A clinical photograph of a skin lesion. Acquired for a research image collection, with no referral diagnosis. A female patient 59 years old: 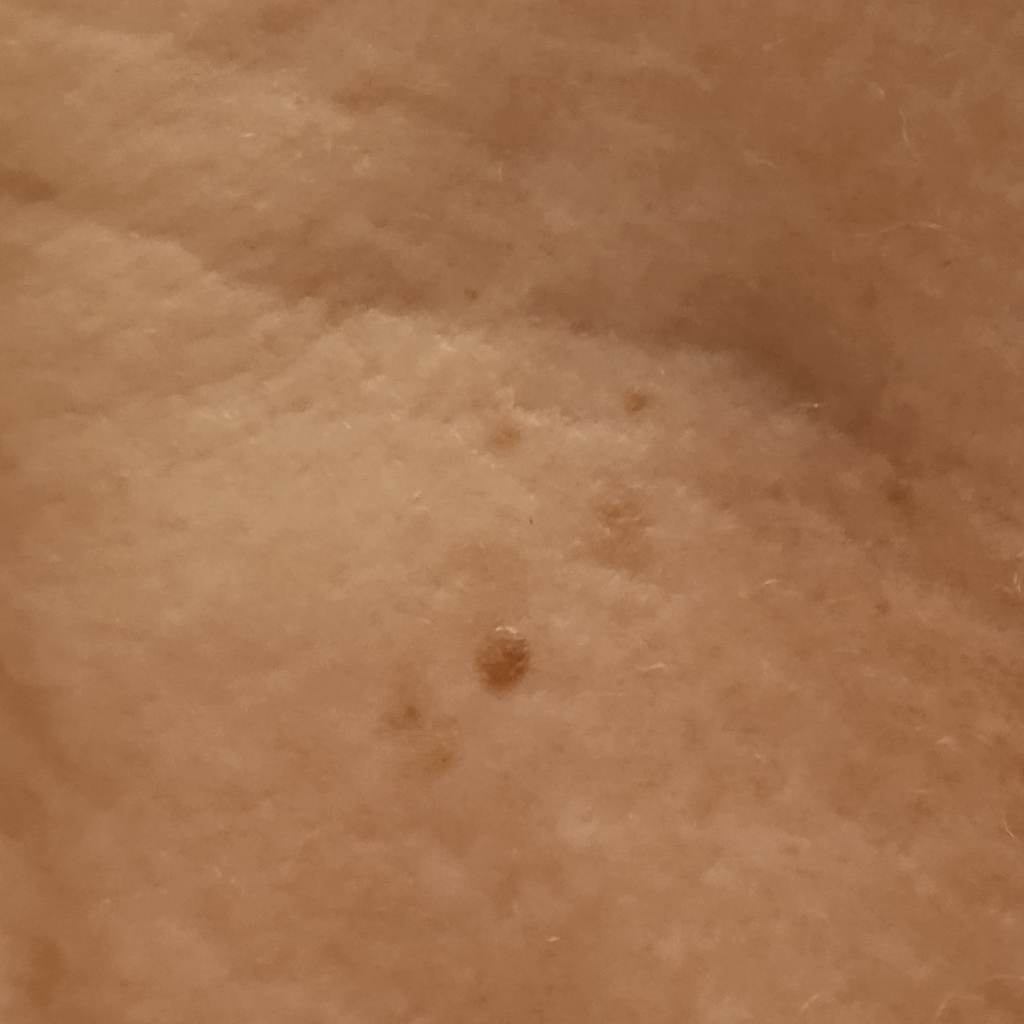Case summary:
The lesion is on the torso. The lesion measures approximately 2.2 mm.
Conclusion:
The consensus diagnosis for this lesion was a seborrheic keratosis.